An image taken at an angle. The affected area is the palm, top or side of the foot, arm, leg and front of the torso. The contributor is a female aged 18–29 — 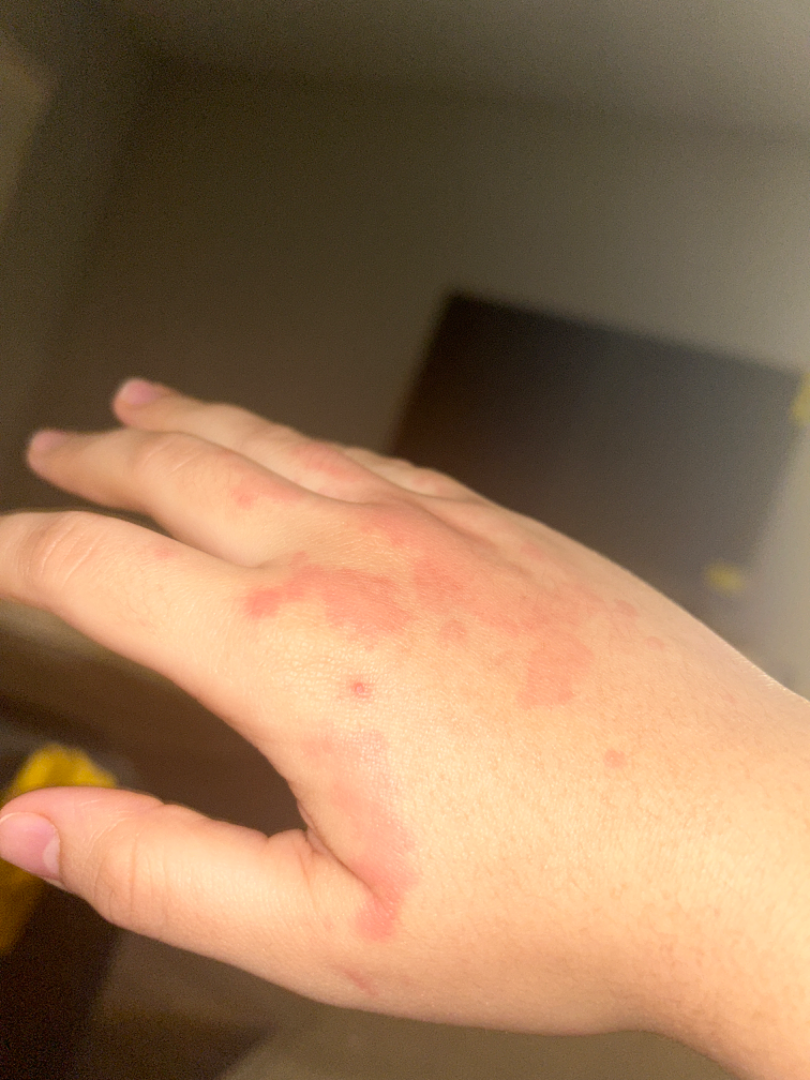assessment — three dermatologists independently reviewed the case: most likely Urticaria; an alternative is Allergic Contact Dermatitis; lower on the differential is Hypersensitivity.